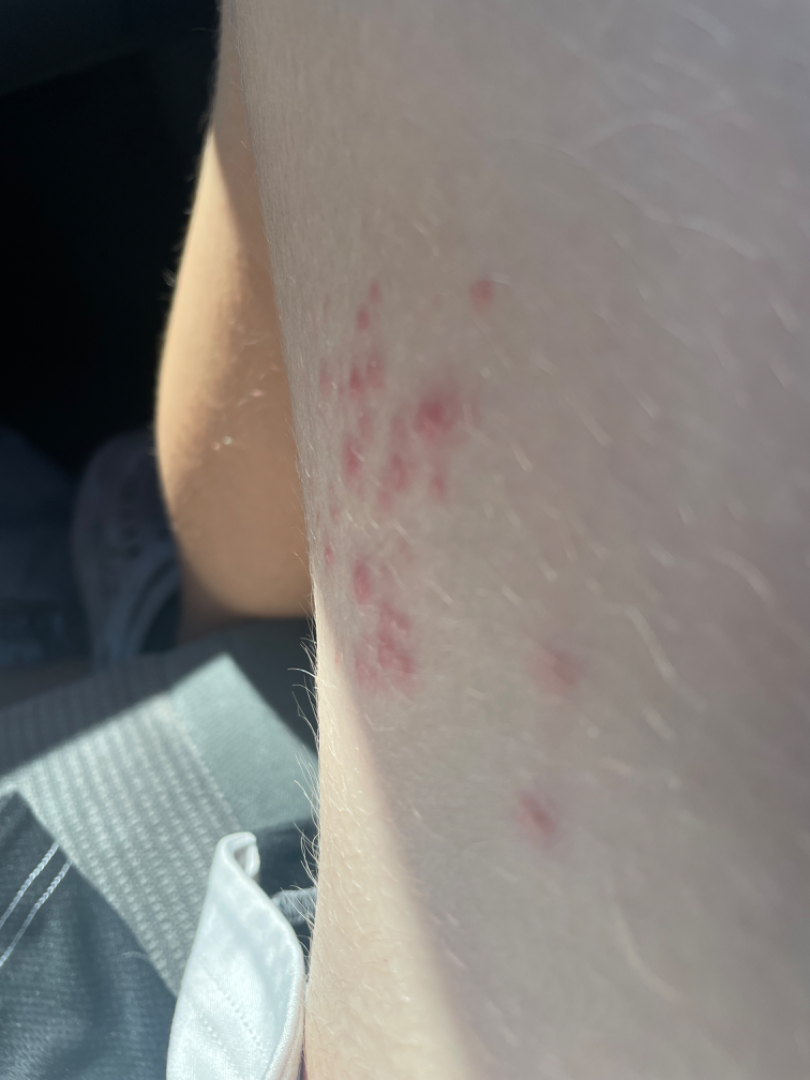The affected area is the leg. The photograph was taken at an angle. One reviewing dermatologist: the impression was split between Folliculitis, Herpes Zoster and Herpes Simplex.